A skin lesion imaged with a dermatoscope.
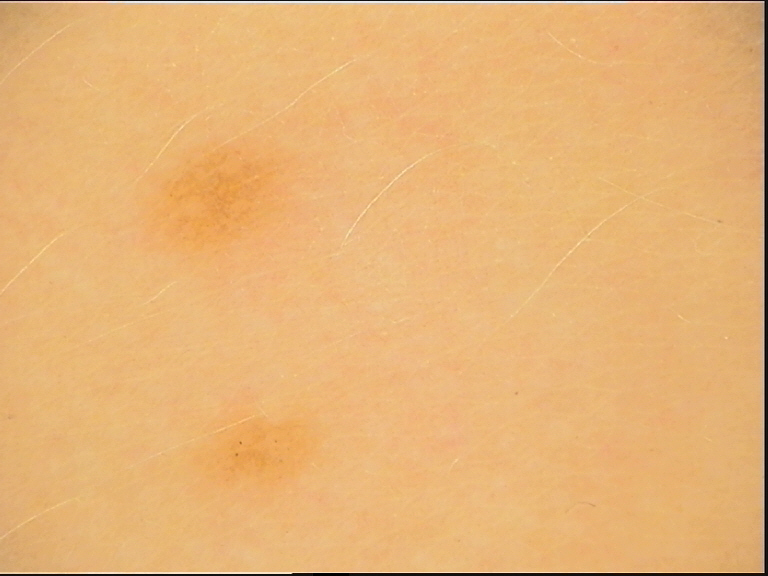Consistent with a dysplastic junctional nevus.